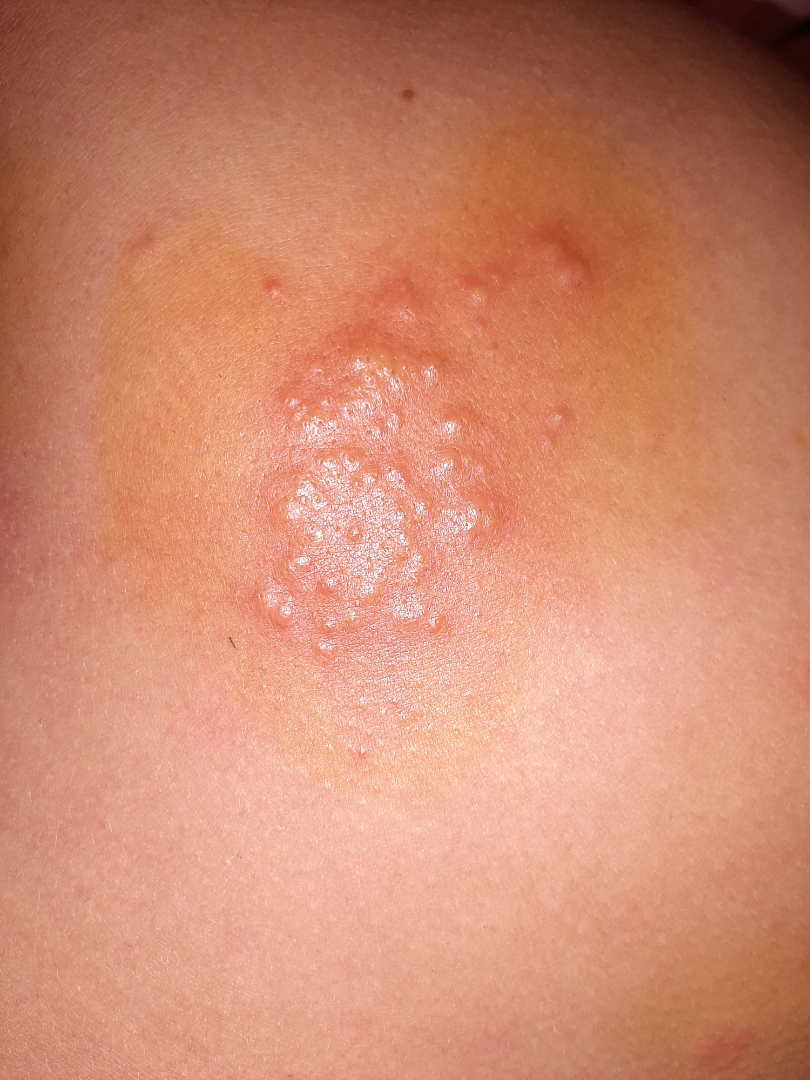The lesion is described as fluid-filled. Skin tone: non-clinician graders estimated Monk skin tone scale 4. No relevant systemic symptoms. The patient notes the condition has been present for less than one week. This is a close-up image. The patient described the issue as a rash. Impetigo and Allergic Contact Dermatitis were considered with similar weight; less probable is Herpes Simplex.